A dermoscopic close-up of a skin lesion.
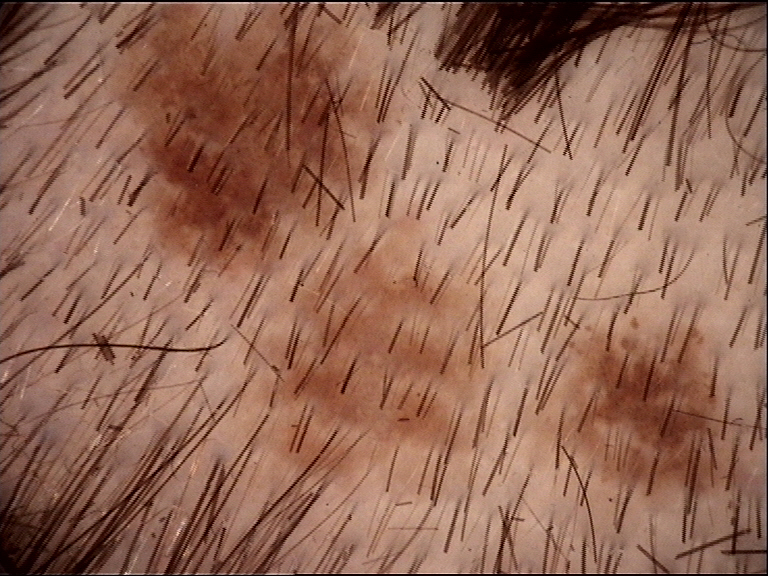Classified as a dysplastic junctional nevus.